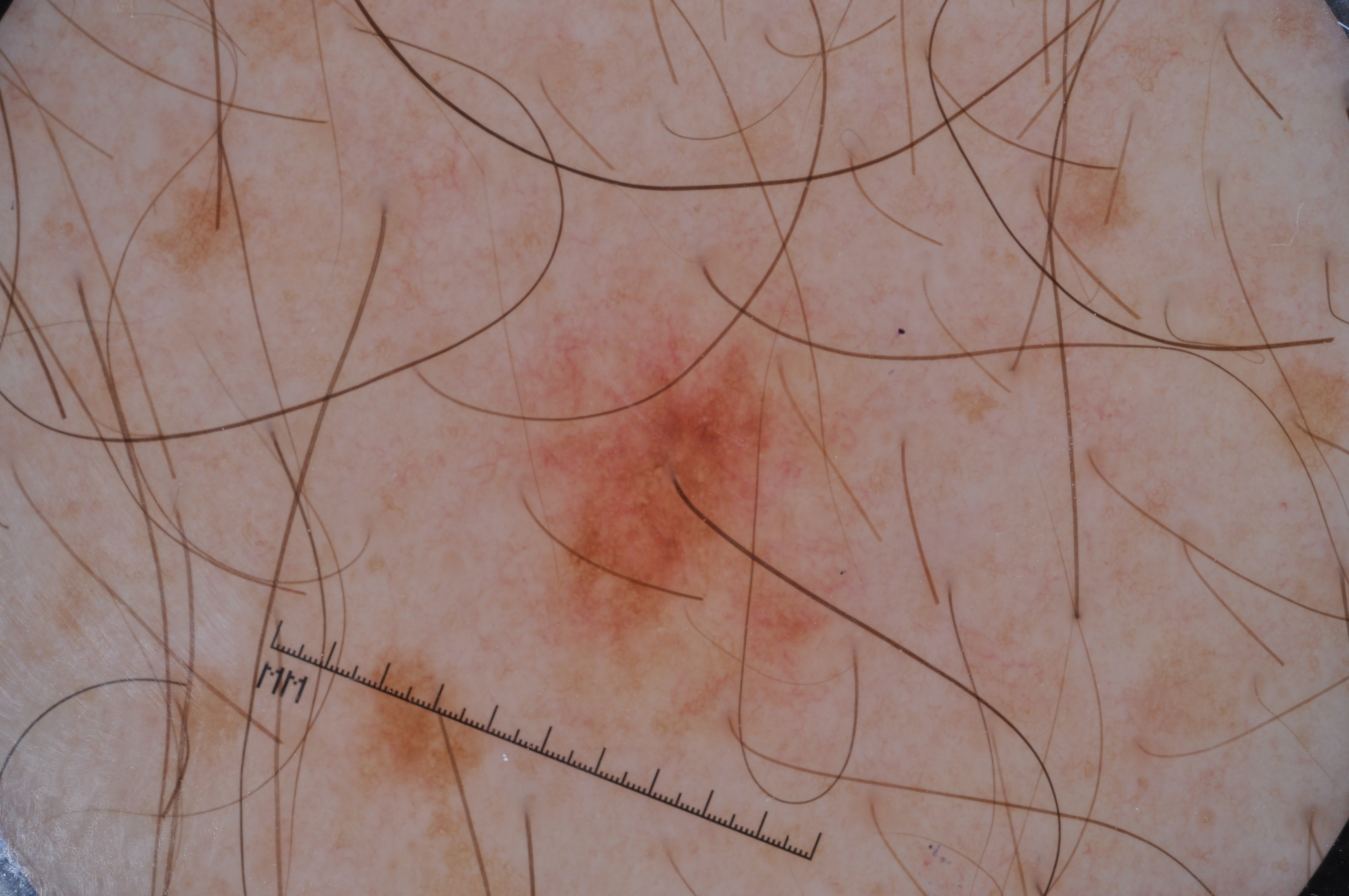Summary: A skin lesion imaged with a dermatoscope. With coordinates (x1, y1, x2, y2), the lesion spans bbox=[461, 252, 898, 761]. Impression: Expert review diagnosed this as a melanocytic nevus, a benign lesion.